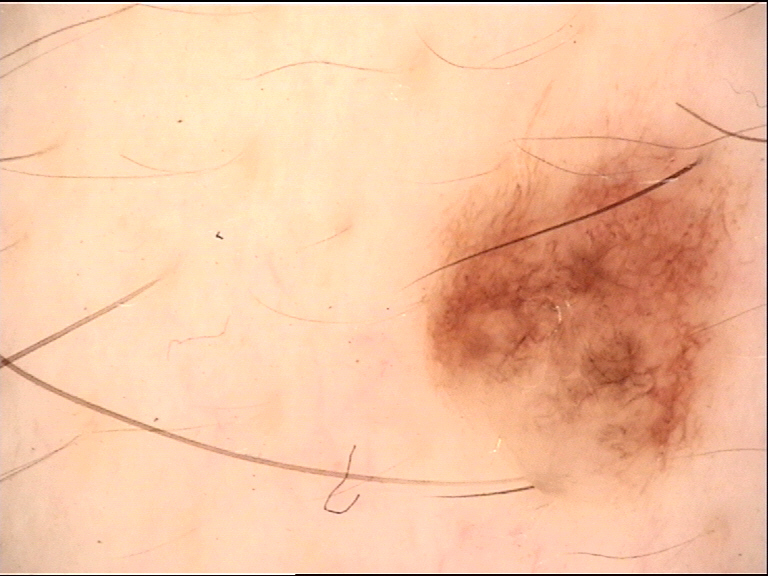<dermoscopy>
  <diagnosis>
    <name>dysplastic junctional nevus</name>
    <code>jd</code>
    <malignancy>benign</malignancy>
    <super_class>melanocytic</super_class>
    <confirmation>expert consensus</confirmation>
  </diagnosis>
</dermoscopy>